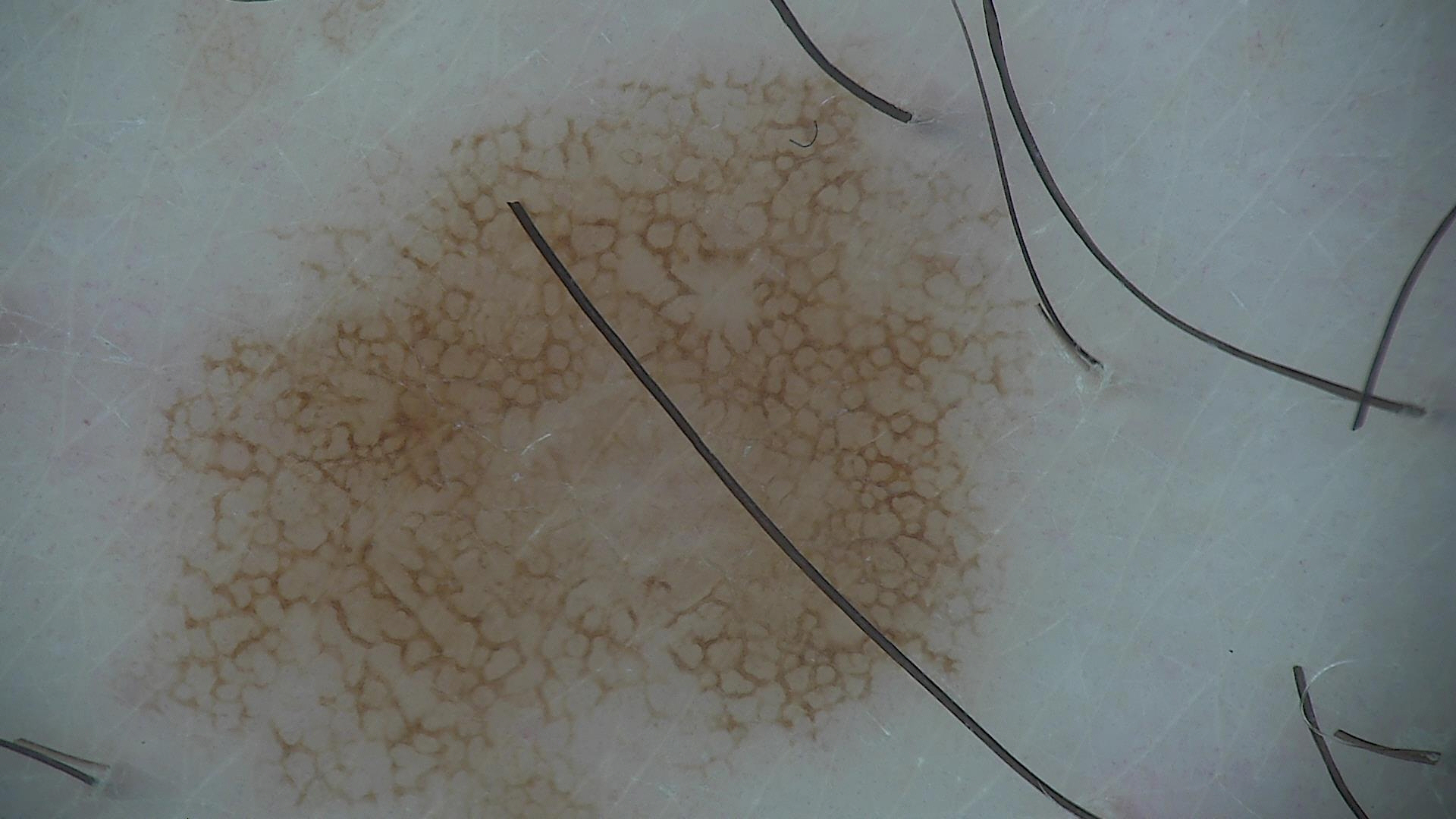Q: What is the diagnosis?
A: dysplastic junctional nevus (expert consensus)